A dermoscopic view of a skin lesion; a female patient, about 30 years old: 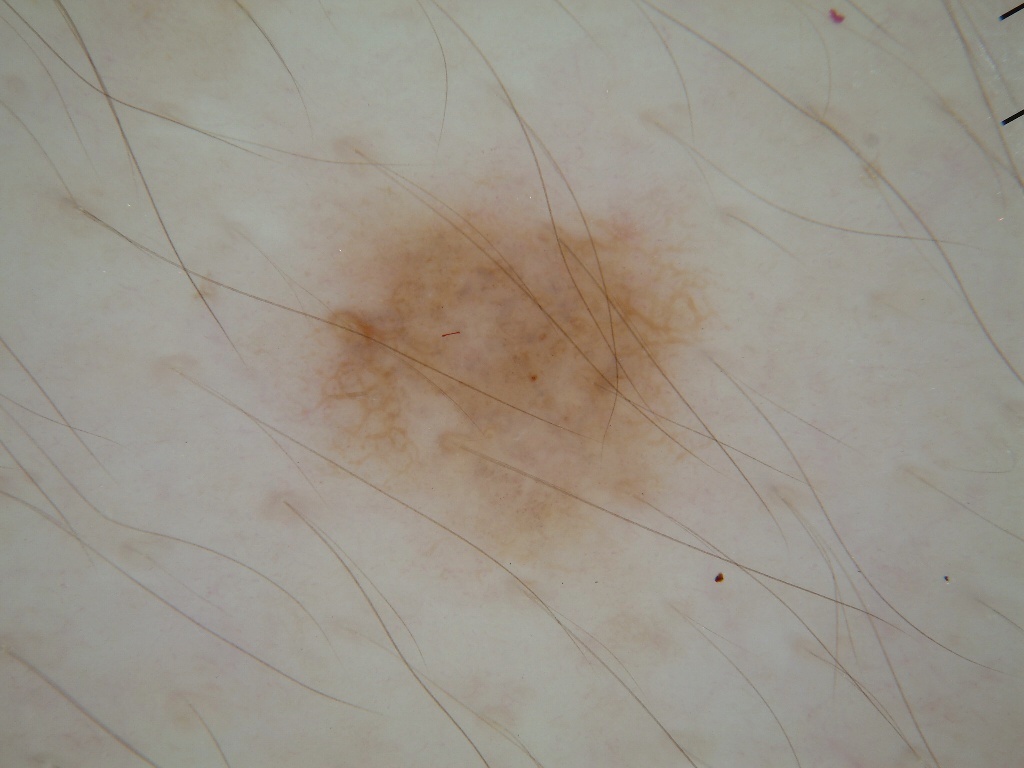dermoscopic_features:
  present:
    - globules
    - pigment network
  absent:
    - streaks
    - negative network
    - milia-like cysts
lesion_location:
  bbox_xyxy:
    - 249
    - 166
    - 740
    - 572
lesion_extent:
  approx_field_fraction_pct: 20
diagnosis:
  name: melanocytic nevus
  malignancy: benign
  lineage: melanocytic
  provenance: clinical